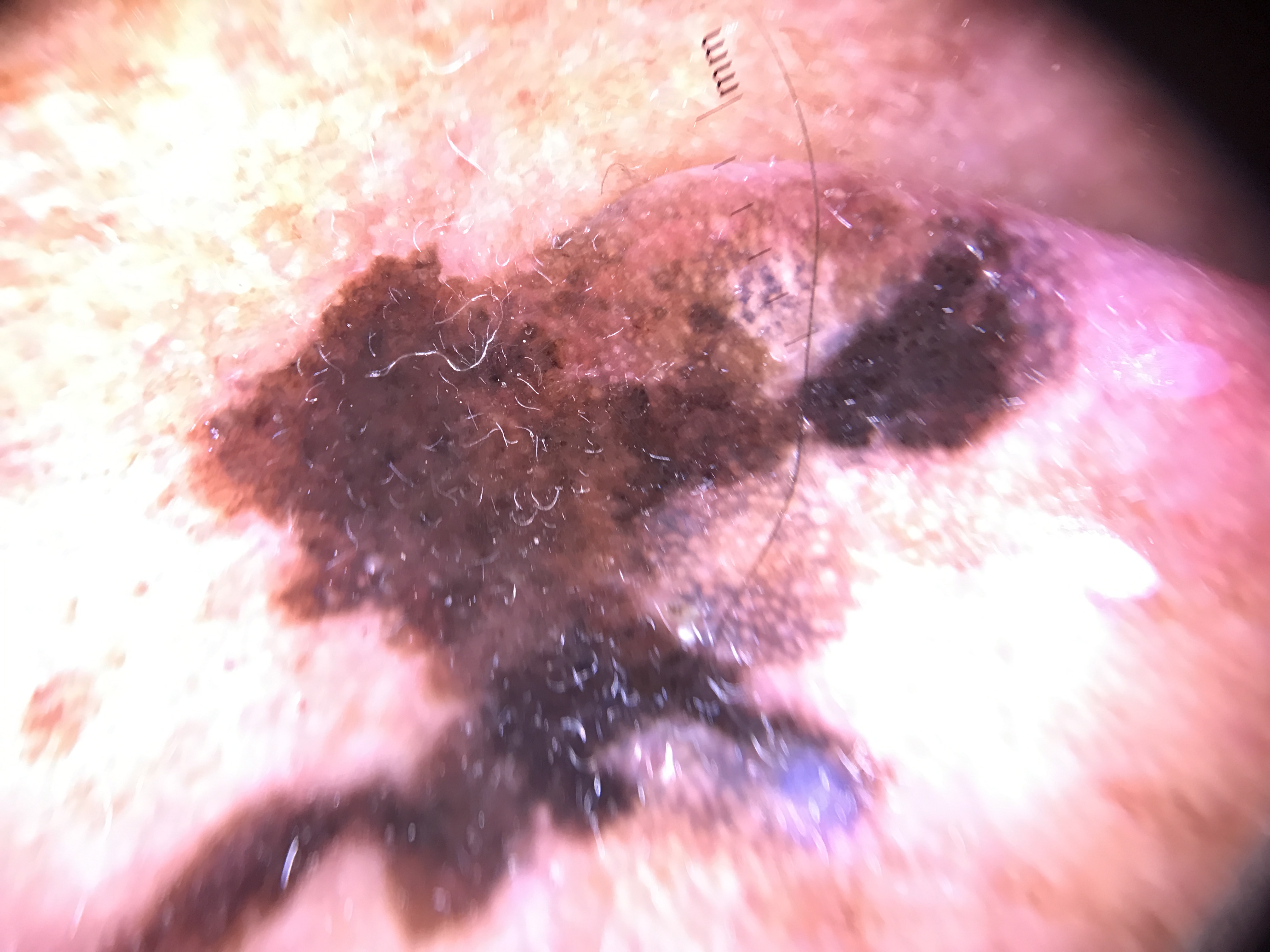Q: What is this lesion?
A: lentigo maligna (biopsy-proven)